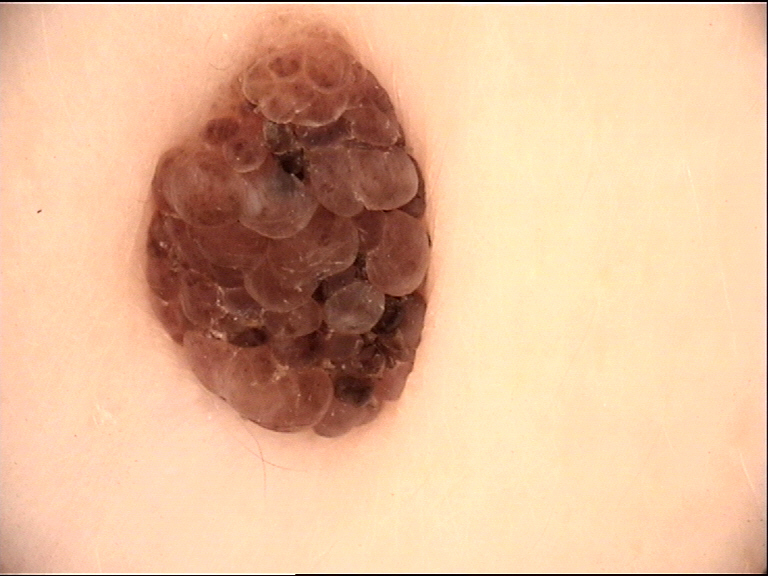modality: dermoscopy
class: dermal nevus (expert consensus)